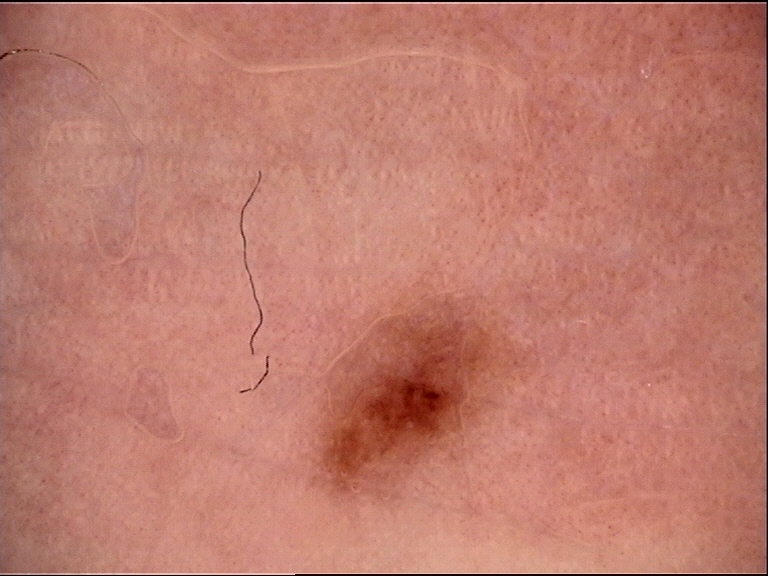diagnostic label = acral dysplastic junctional nevus (expert consensus).